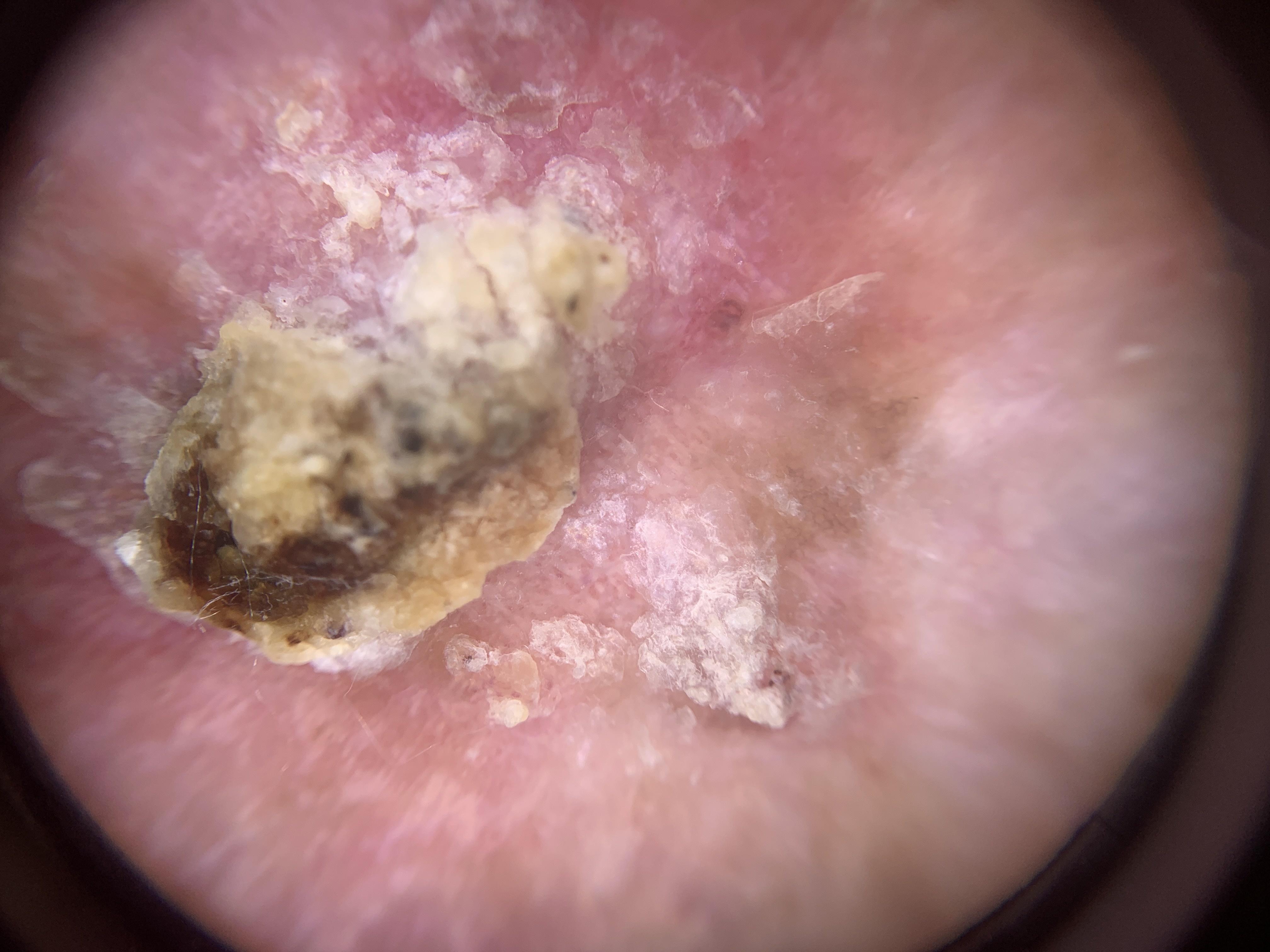skin phototype: II
imaging: contact-polarized dermoscopy
subject: female, aged around 85 or older
body site: a lower extremity
diagnostic label: Squamous cell carcinoma (biopsy-proven)